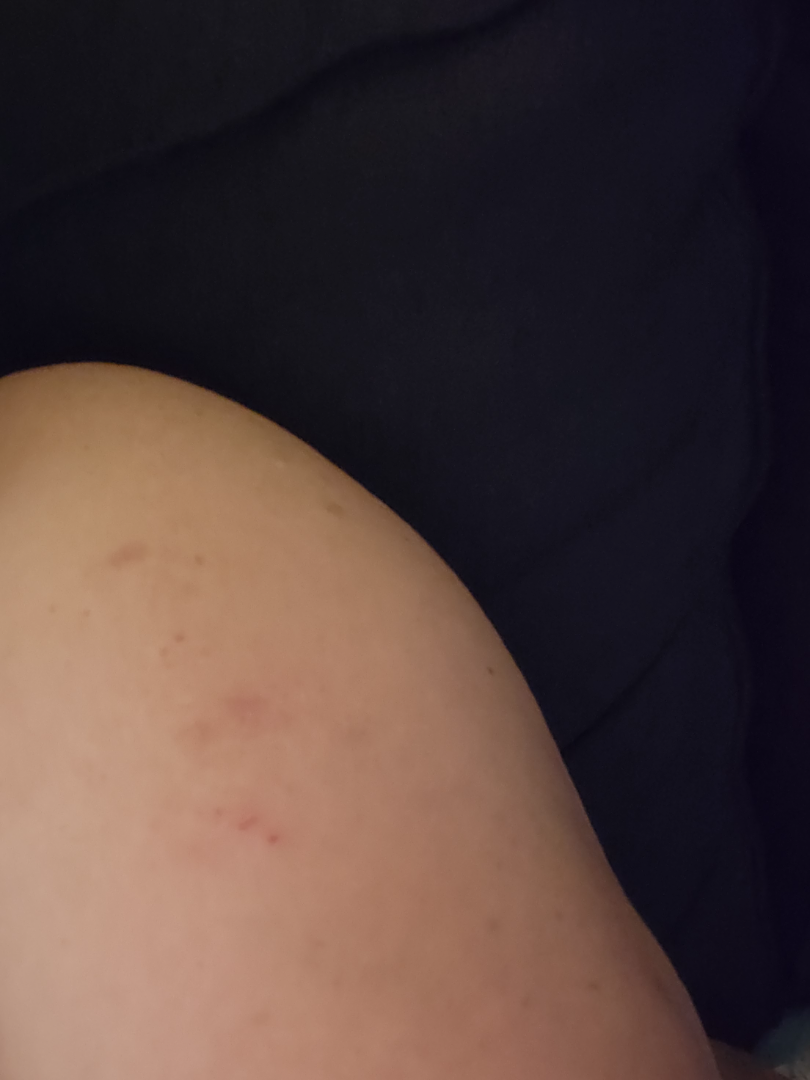assessment=not assessable
patient=female, age 50–59
image framing=at an angle
patient describes the issue as=a rash
onset=more than one year
site=arm
symptoms=bothersome appearance and itching